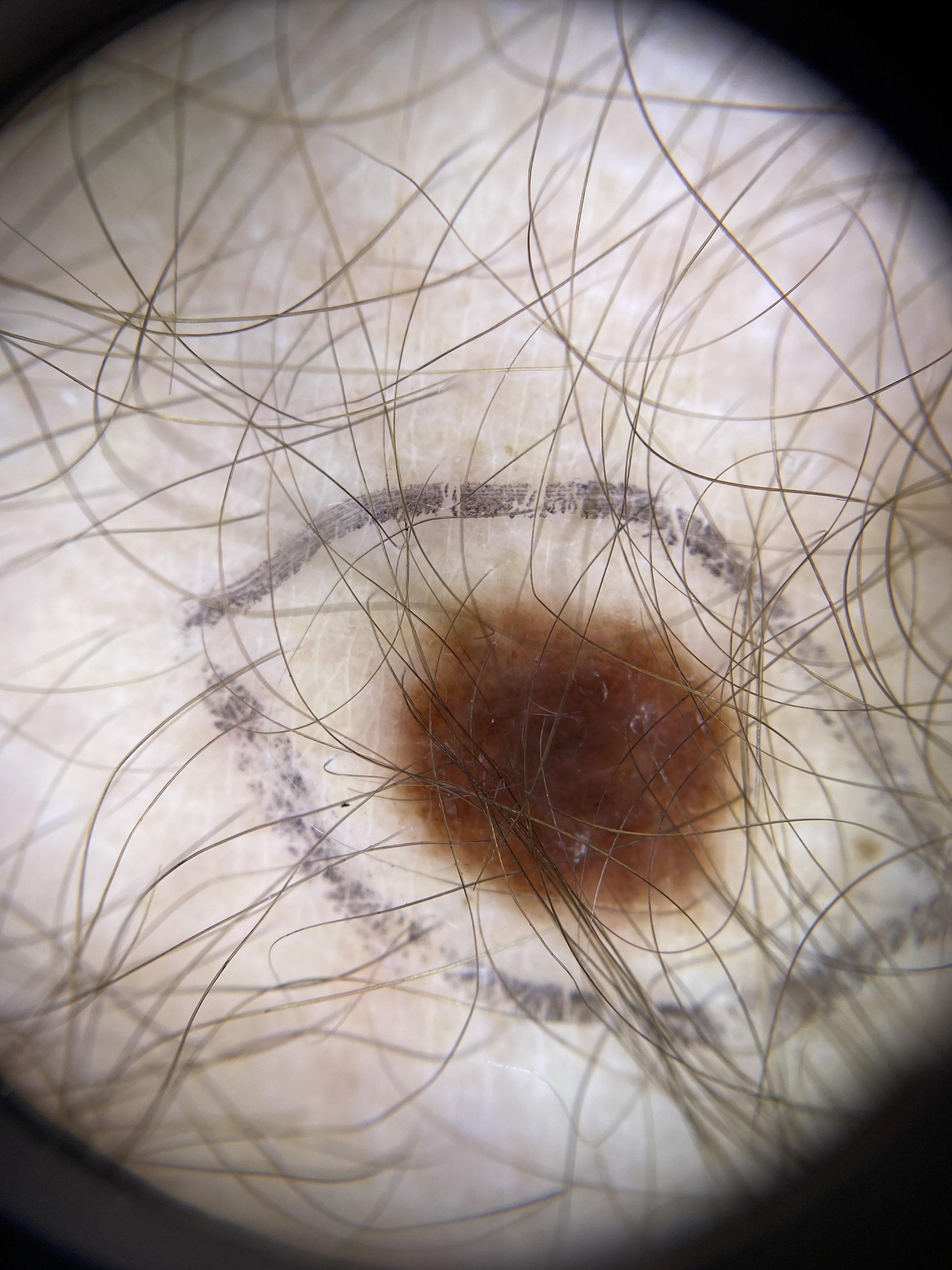The biopsy diagnosis was a nevus.